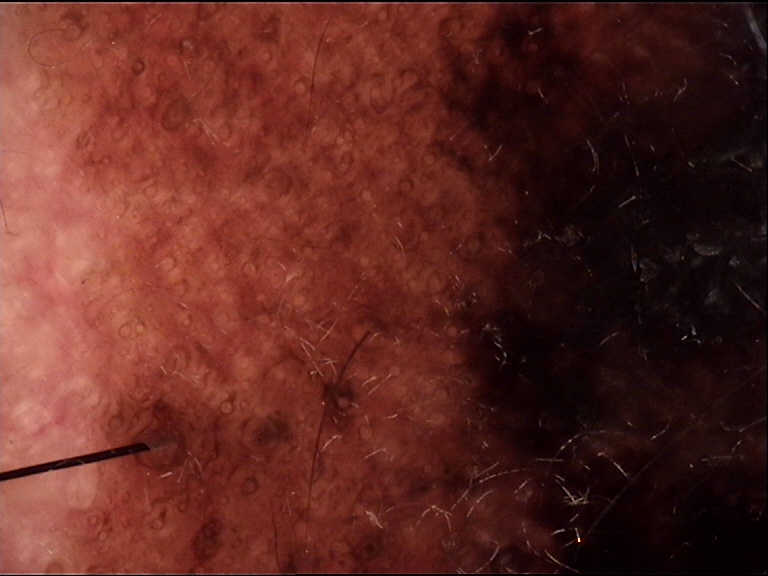image type: dermatoscopy, pathology: lentigo maligna (biopsy-proven).